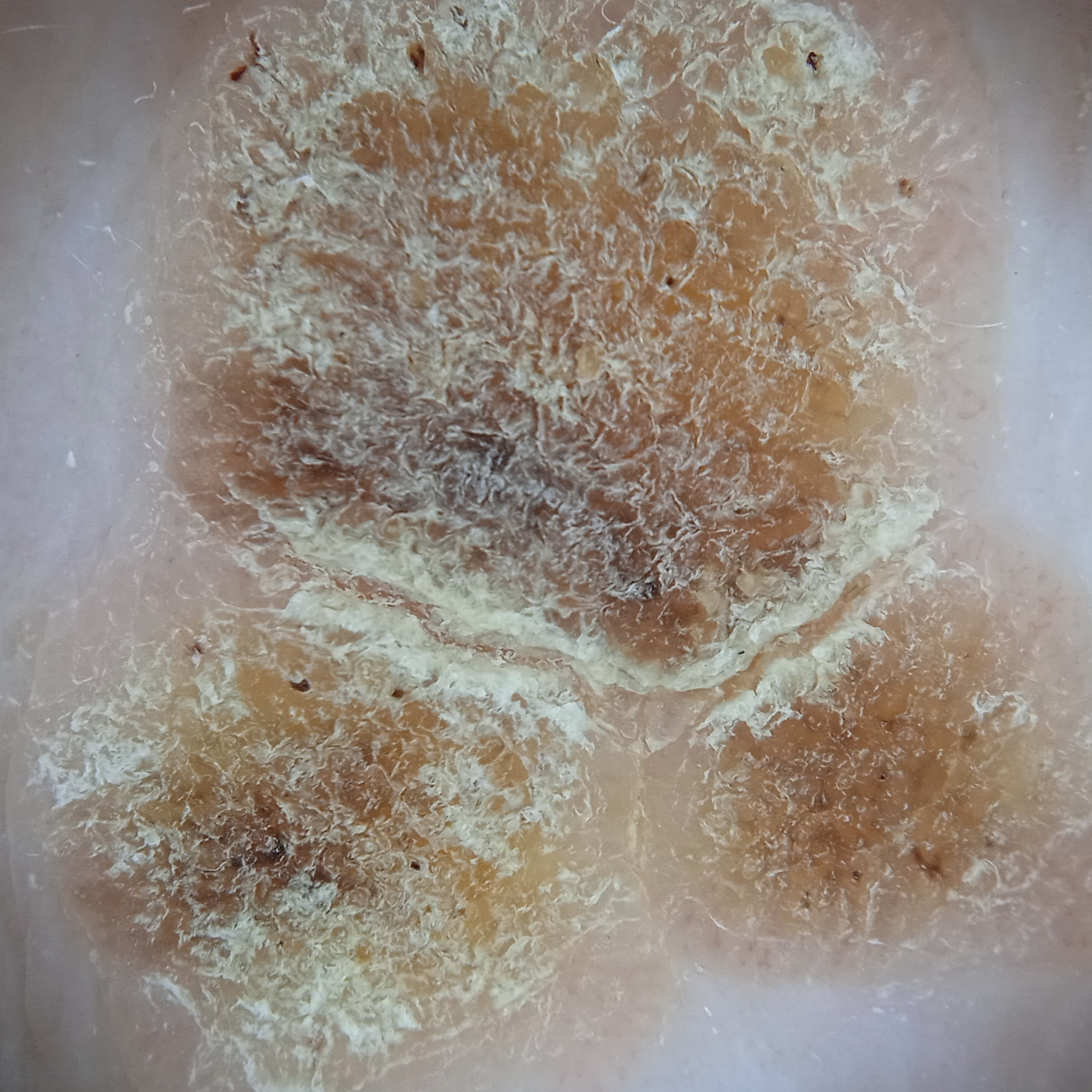A male patient age 77. The patient reports a personal history of cancer and a personal history of skin cancer. The patient says their skin reddens with sun exposure. The patient describes having a moderate number of moles. Imaged for a research study, with no referral diagnosis recorded. A dermoscopy image of a skin lesion. The lesion is on the back. Measuring roughly 14.2 mm. Reviewed by four dermatologists, the consensus diagnosis was a seborrheic keratosis; the reviewers were not unanimous; an alternative consideration was a squamous cell carcinoma.